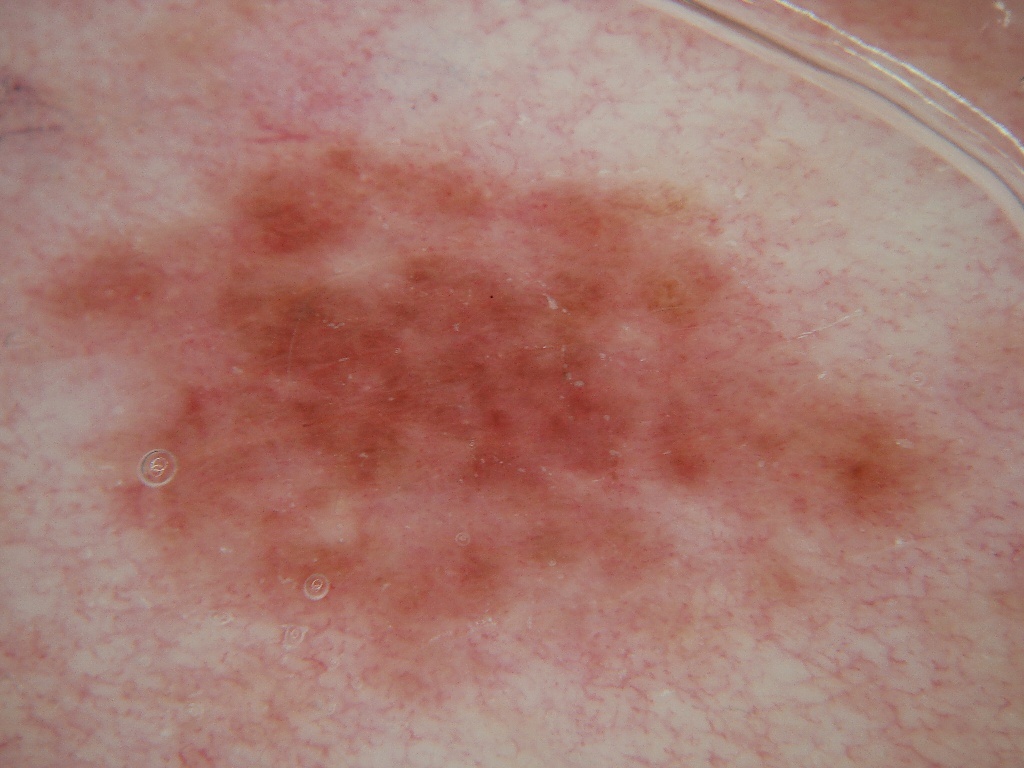{
  "image": {
    "modality": "dermoscopy"
  },
  "patient": {
    "sex": "male",
    "age_approx": 60
  },
  "lesion_location": {
    "bbox_xyxy": [
      31,
      135,
      966,
      657
    ]
  },
  "dermoscopic_features": {
    "present": [],
    "absent": [
      "negative network",
      "milia-like cysts",
      "globules",
      "streaks",
      "pigment network"
    ]
  },
  "diagnosis": {
    "name": "melanocytic nevus",
    "malignancy": "benign",
    "lineage": "melanocytic",
    "provenance": "clinical"
  }
}